The lesion involves the front of the torso and arm, close-up view: 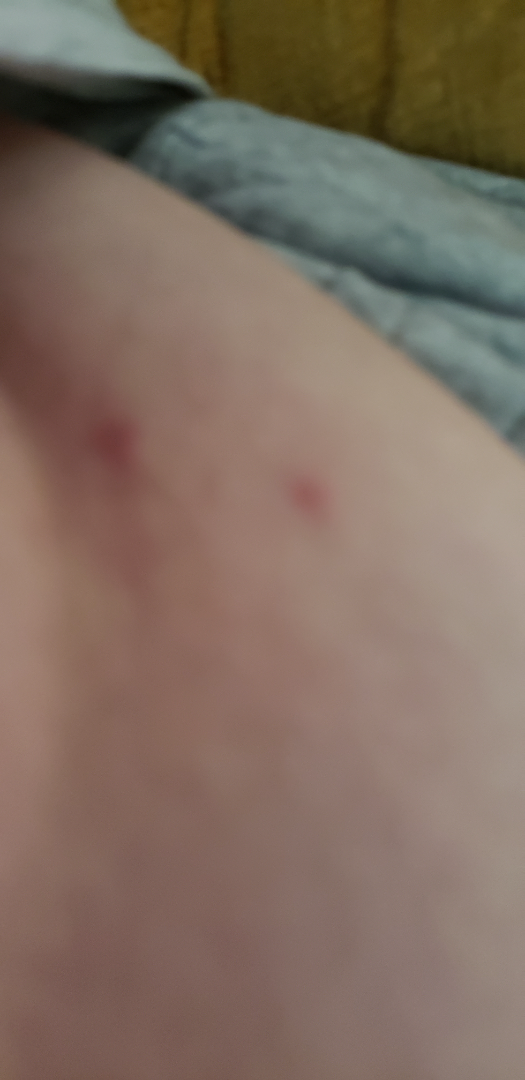assessment: could not be assessed.